Dermoscopy of a skin lesion:
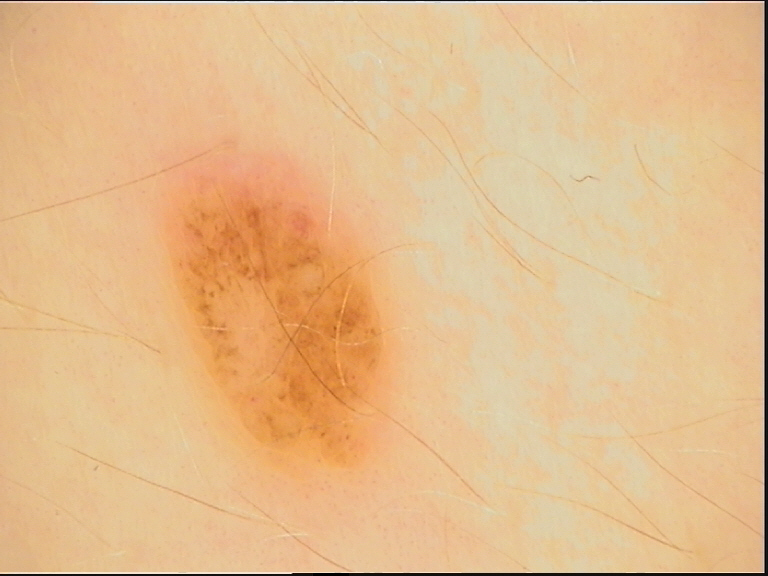Labeled as a banal lesion — a compound nevus.